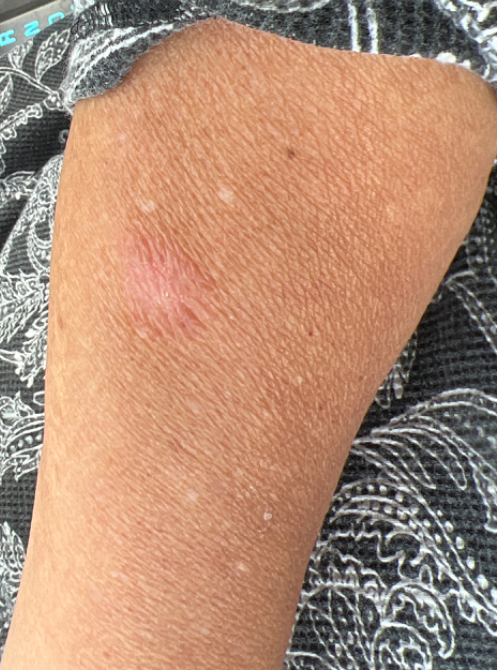The reviewing dermatologist was unable to assign a differential diagnosis from the image.
Female subject, age 50–59.
This image was taken at a distance.
The lesion is described as raised or bumpy.